The affected area is the leg. Texture is reported as raised or bumpy. The patient is male. Self-categorized by the patient as a rash. This is a close-up image. Reported duration is about one day. The contributor notes itching.
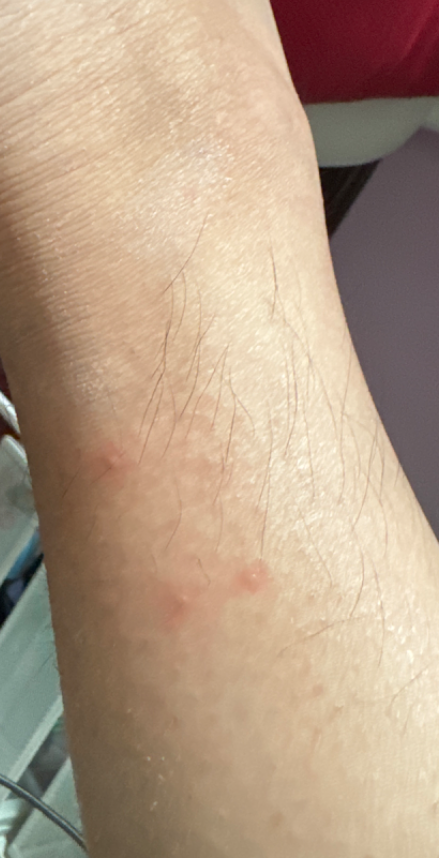Review: The reviewing clinician's impression was: in keeping with Insect Bite.